Close-up view — 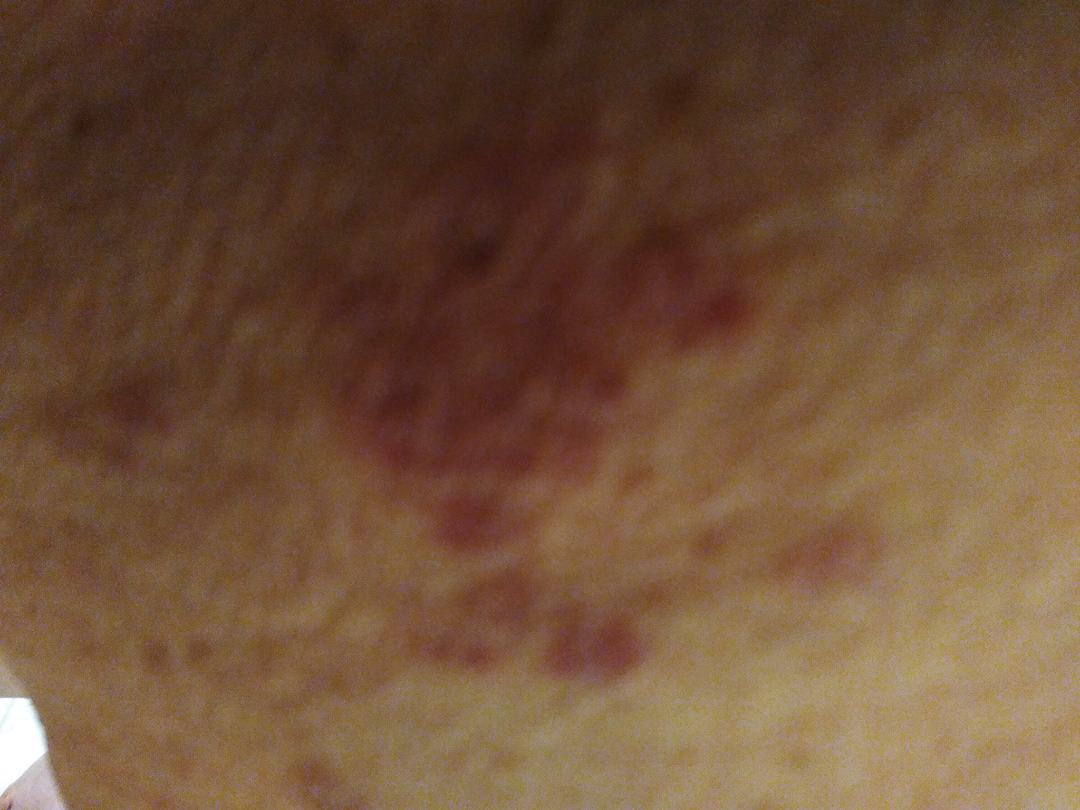assessment: could not be assessed.